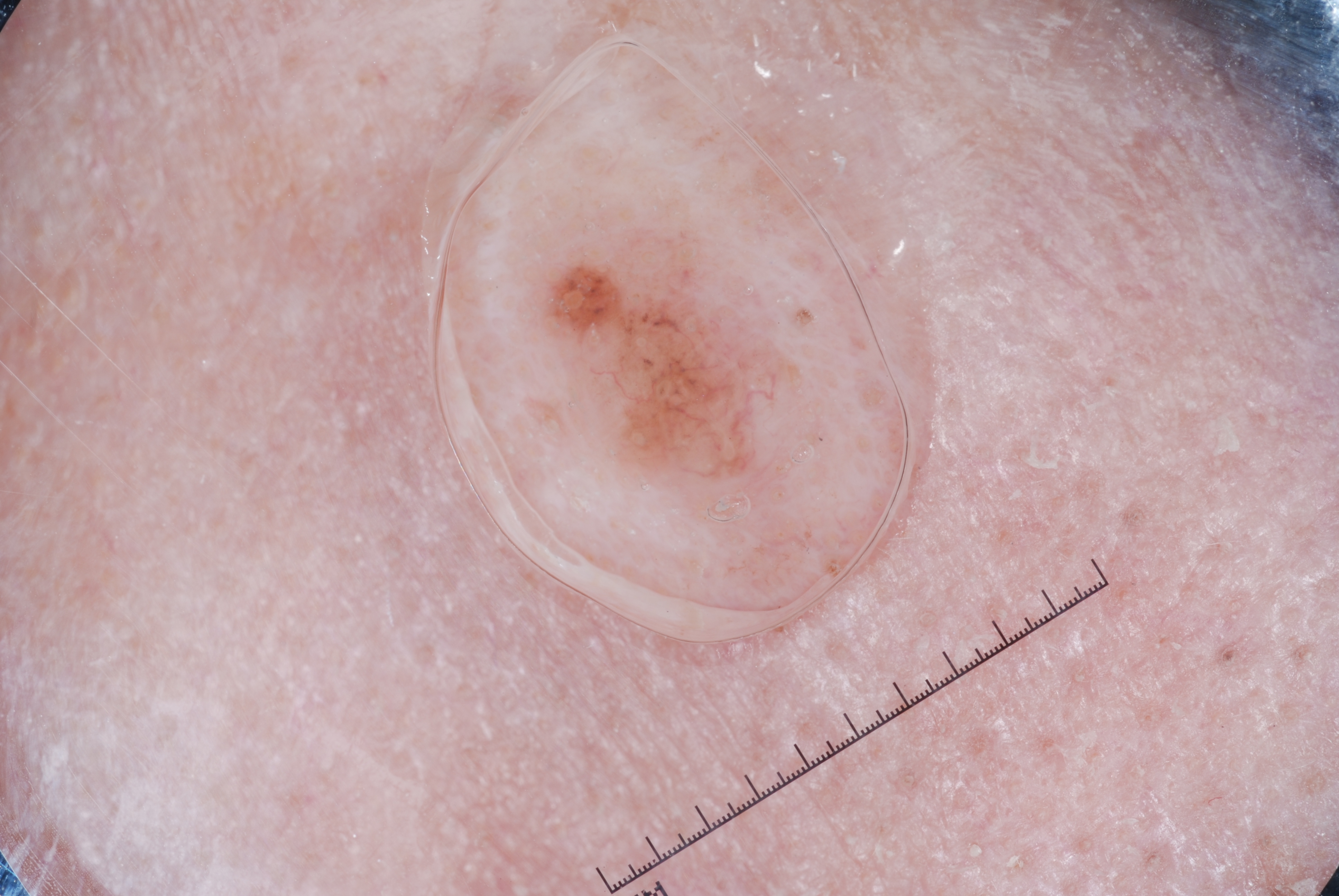subject=female, aged approximately 60 | modality=dermoscopic image | lesion bbox=555 259 764 476 | features=milia-like cysts; absent: pigment network, negative network, and streaks | diagnosis=a melanocytic nevus.